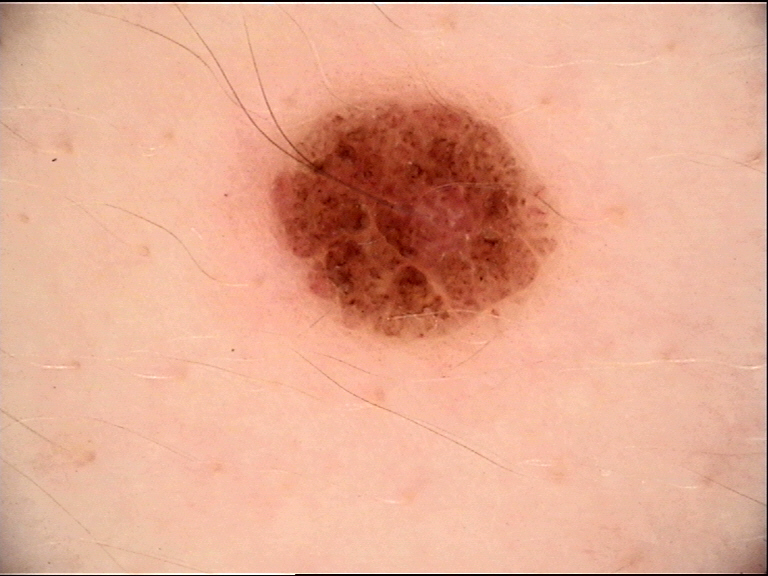A dermoscopic image of a skin lesion. The diagnosis was a banal lesion — a compound nevus.